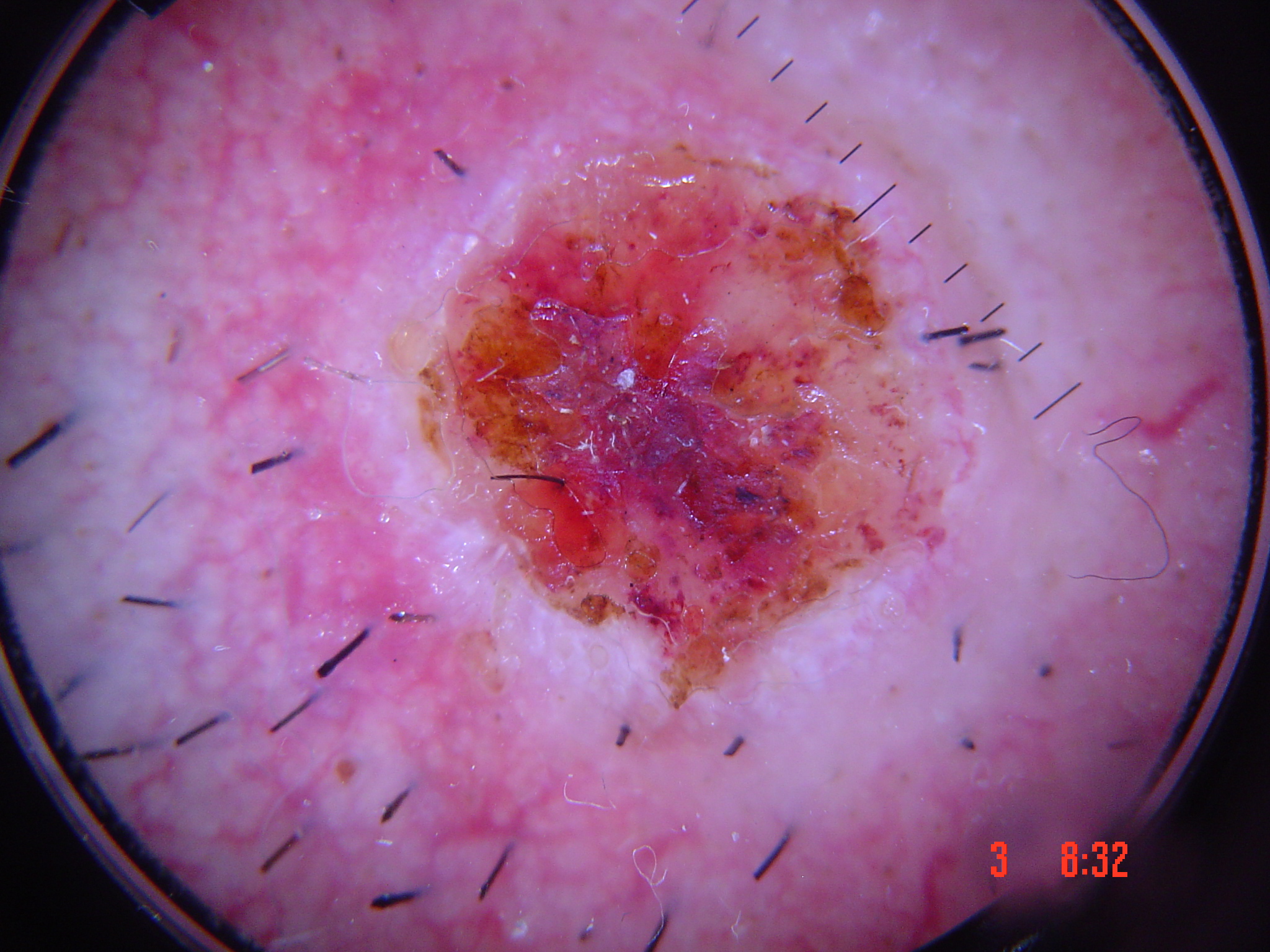Histopathologically confirmed as a skin cancer — a squamous cell carcinoma.